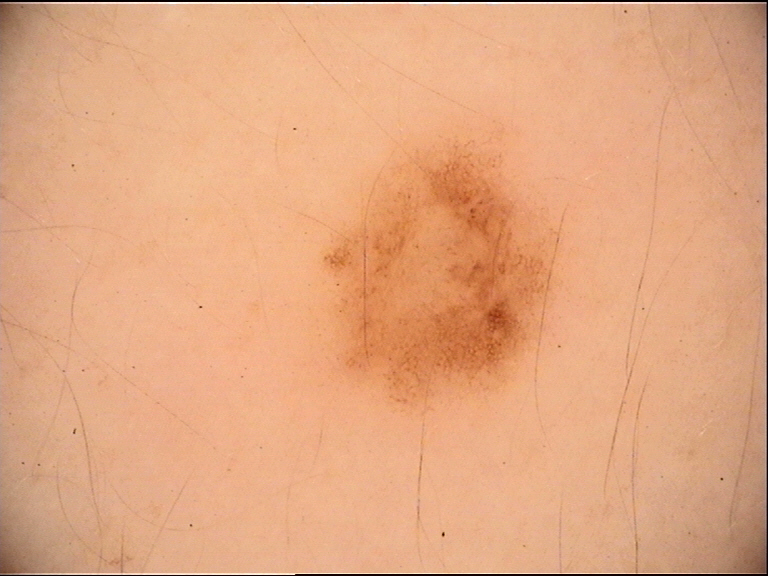Conclusion:
Consistent with a benign lesion — a dysplastic junctional nevus.